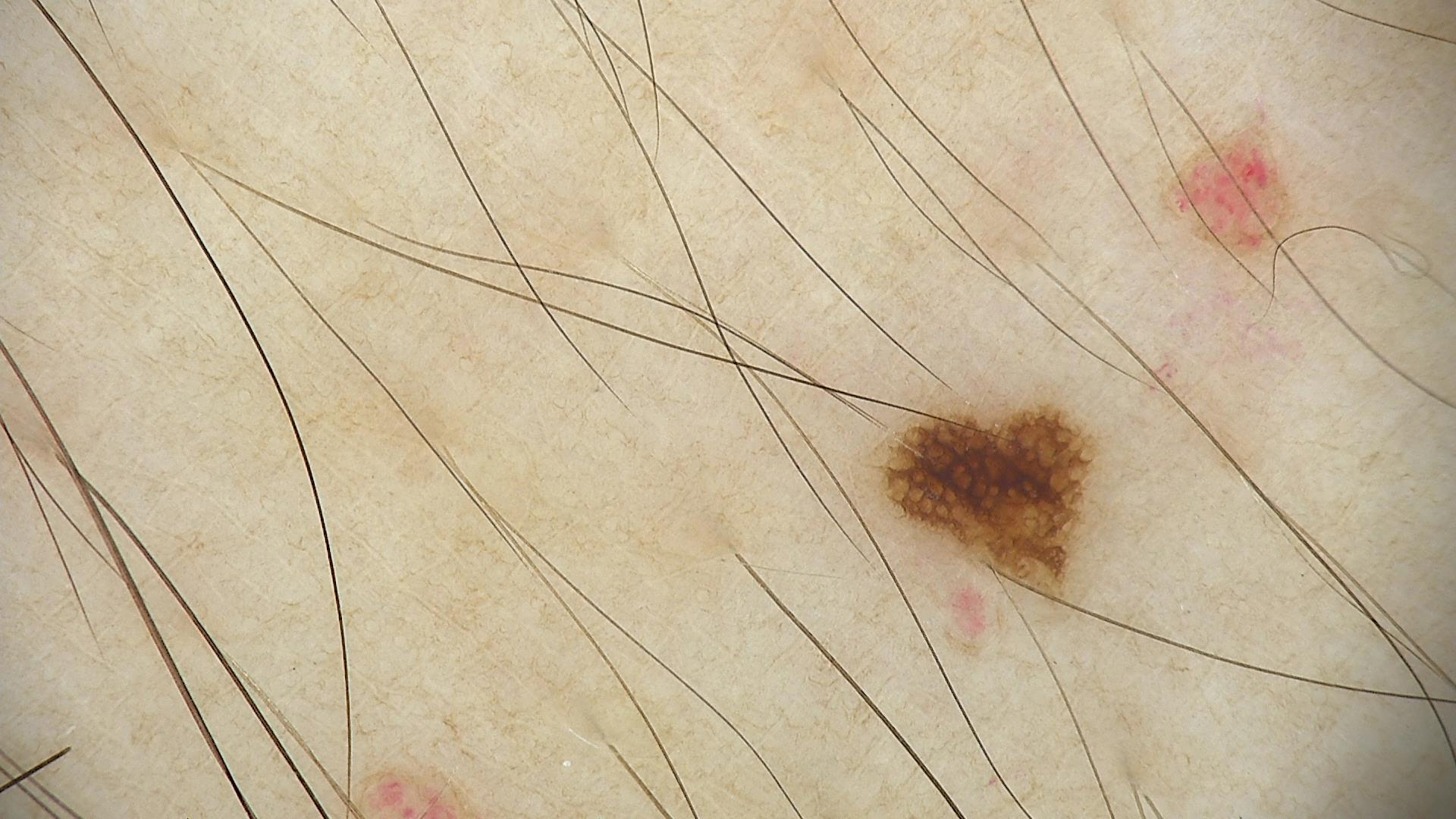The diagnosis was a dysplastic junctional nevus.